The photograph is a close-up of the affected area, FST II; non-clinician graders estimated MST 1 or 2 (two reviewer pools).
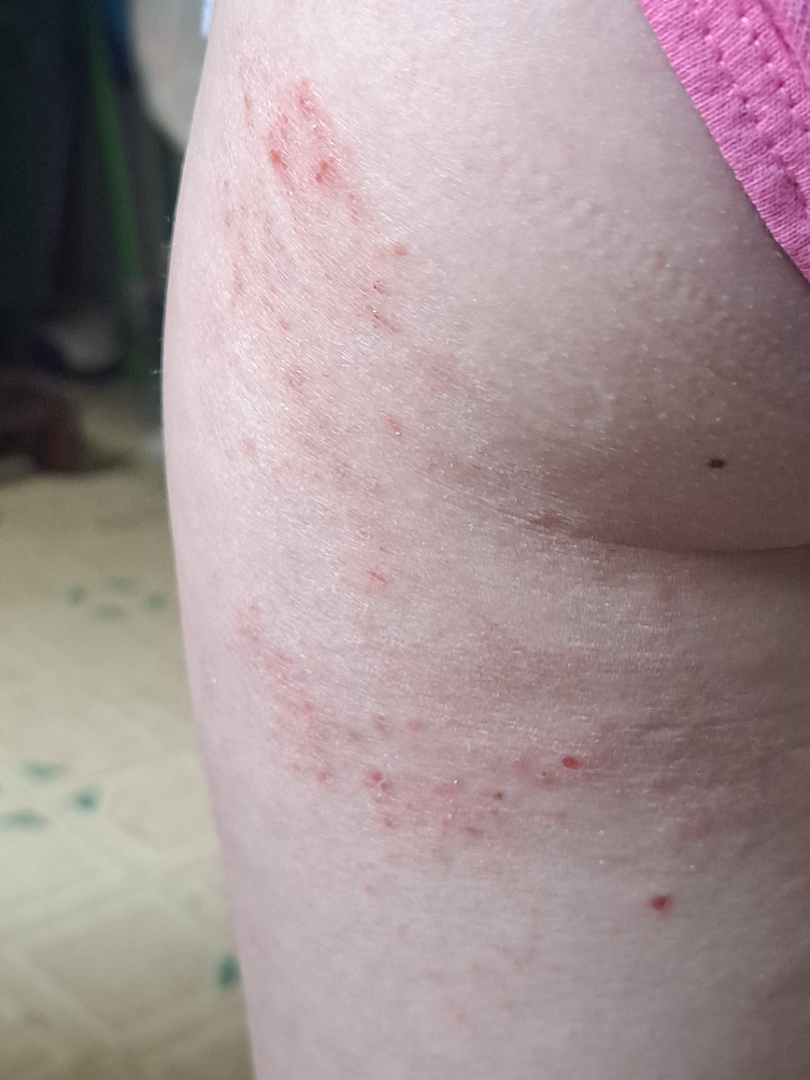impression = the favored diagnosis is Tinea; also raised was Eczema; a remote consideration is Irritant Contact Dermatitis